The affected area is the arm, back of the torso, leg and head or neck · the photograph was taken at an angle: 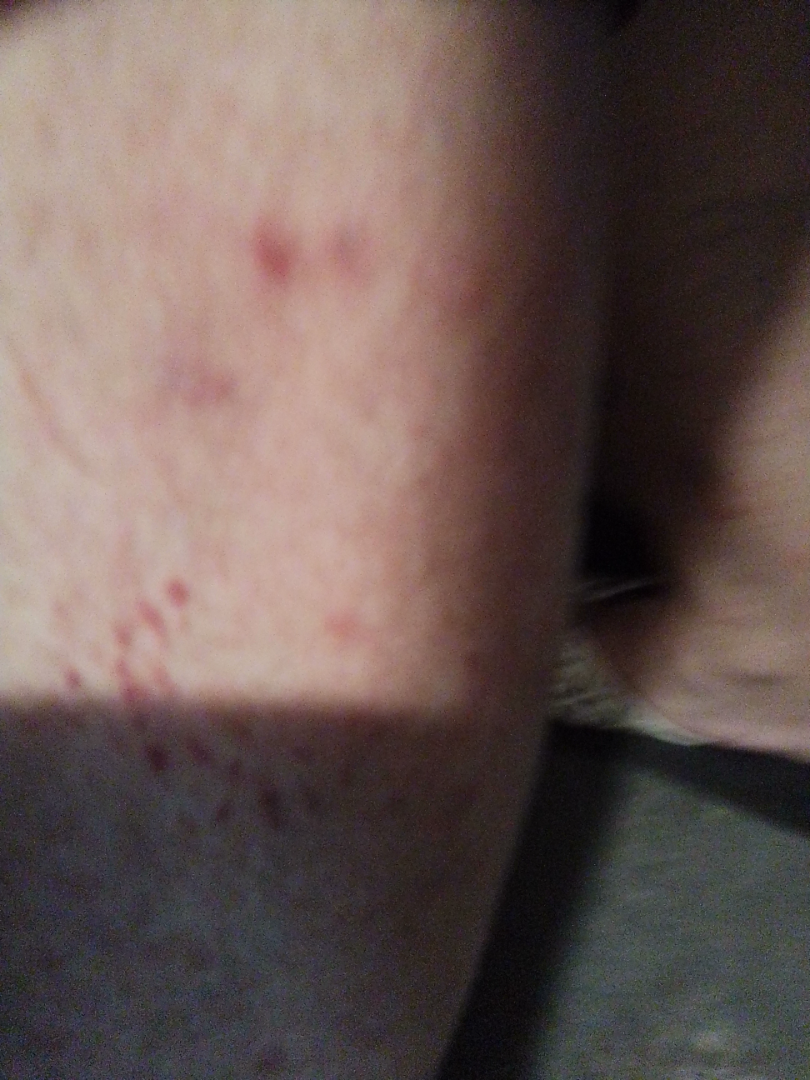| feature | finding |
|---|---|
| assessment | ungradable on photographic review |